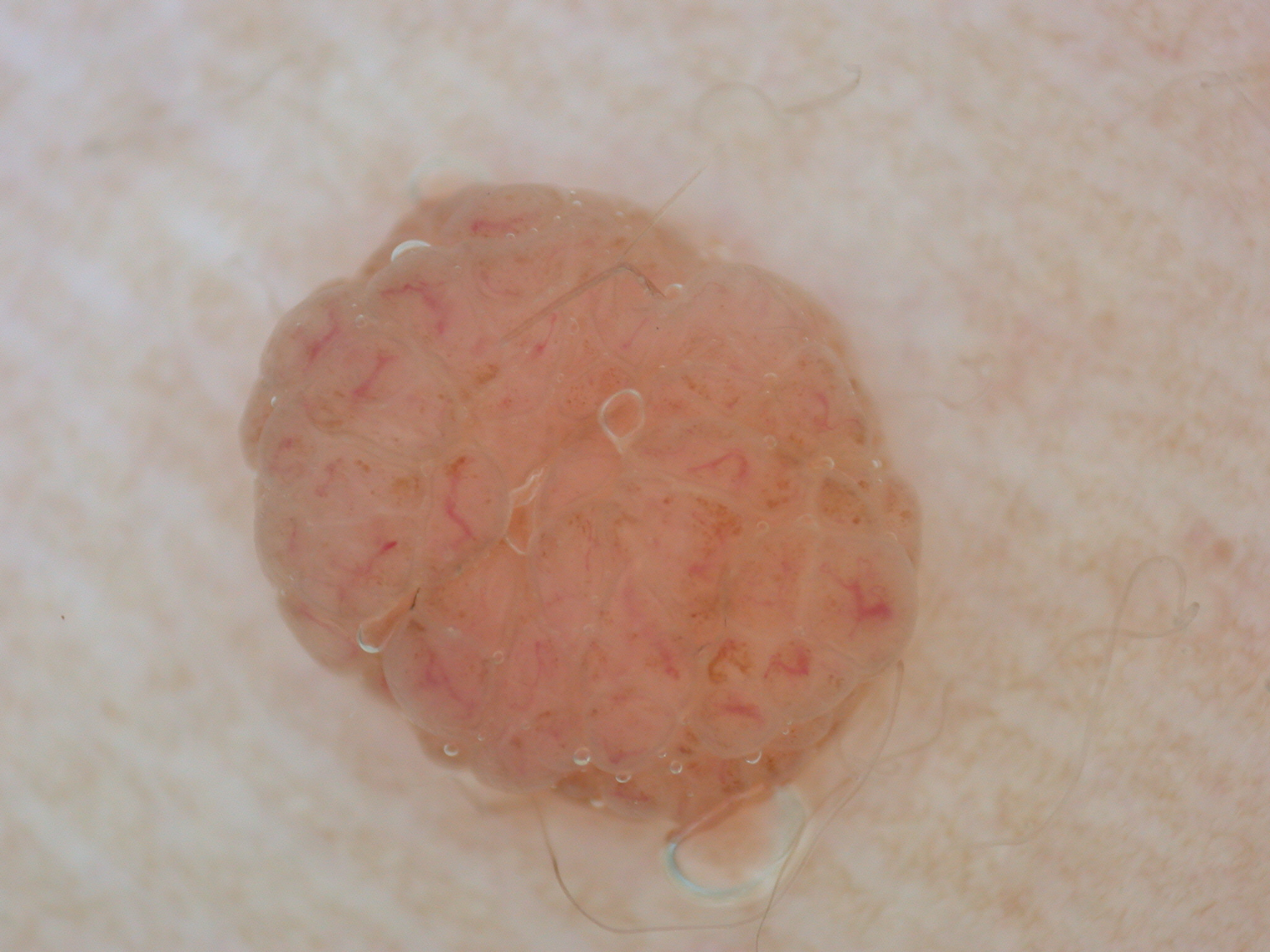A dermoscopic image of a skin lesion. As (left, top, right, bottom), the visible lesion spans [237,180,921,842]. Dermoscopic assessment notes no streaks, negative network, pigment network, milia-like cysts, or globules. The clinical diagnosis was a melanocytic nevus, a benign lesion.